A skin lesion imaged with a dermatoscope.
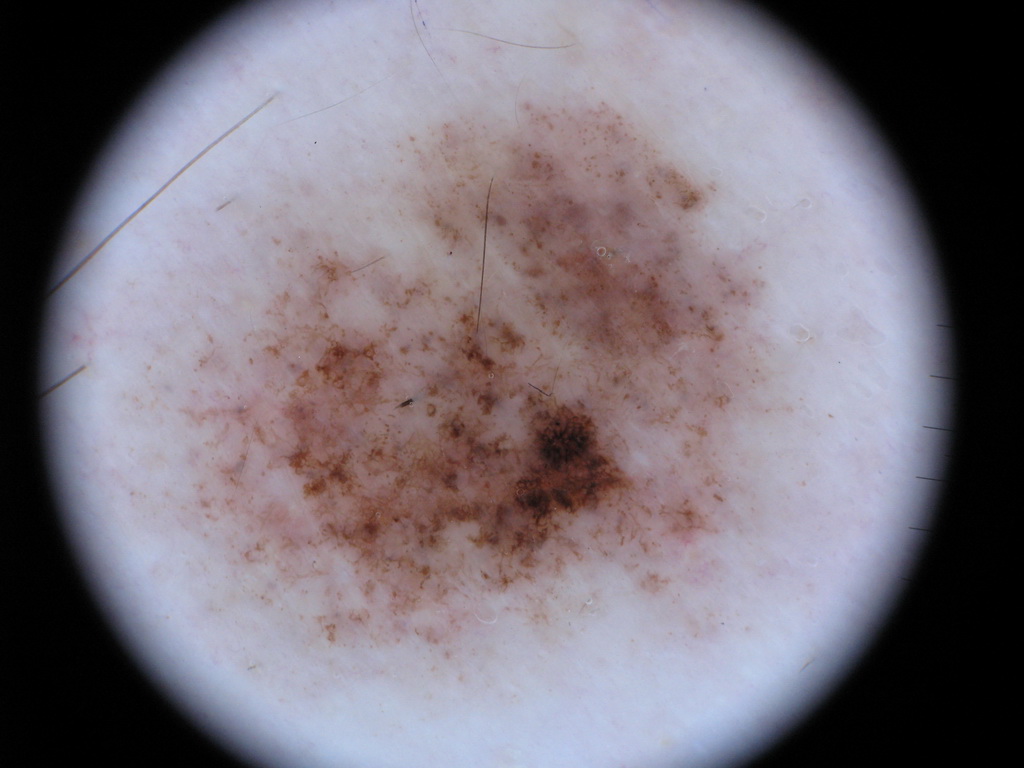– lesion bbox: bbox=[115, 78, 838, 701]
– assessment: a melanoma